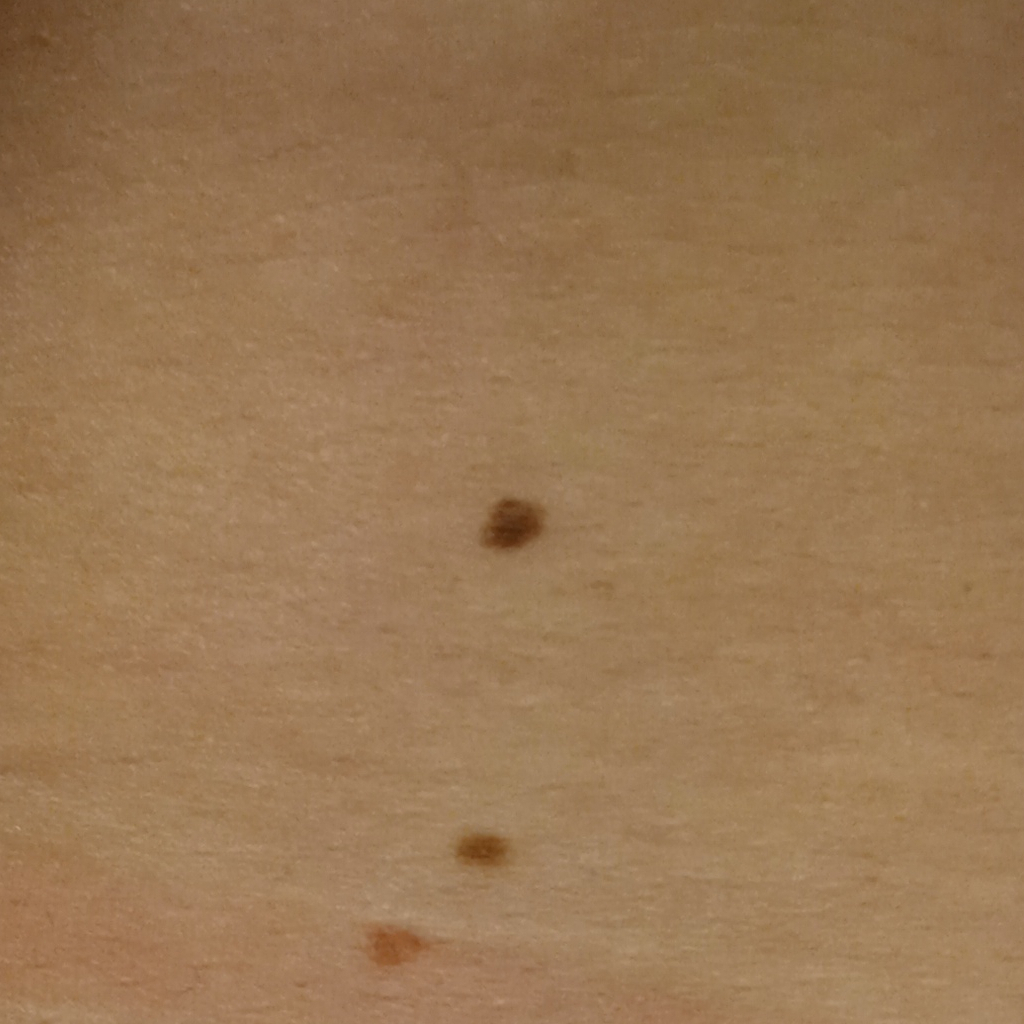Impression:
The consensus diagnosis for this lesion was a melanocytic nevus.